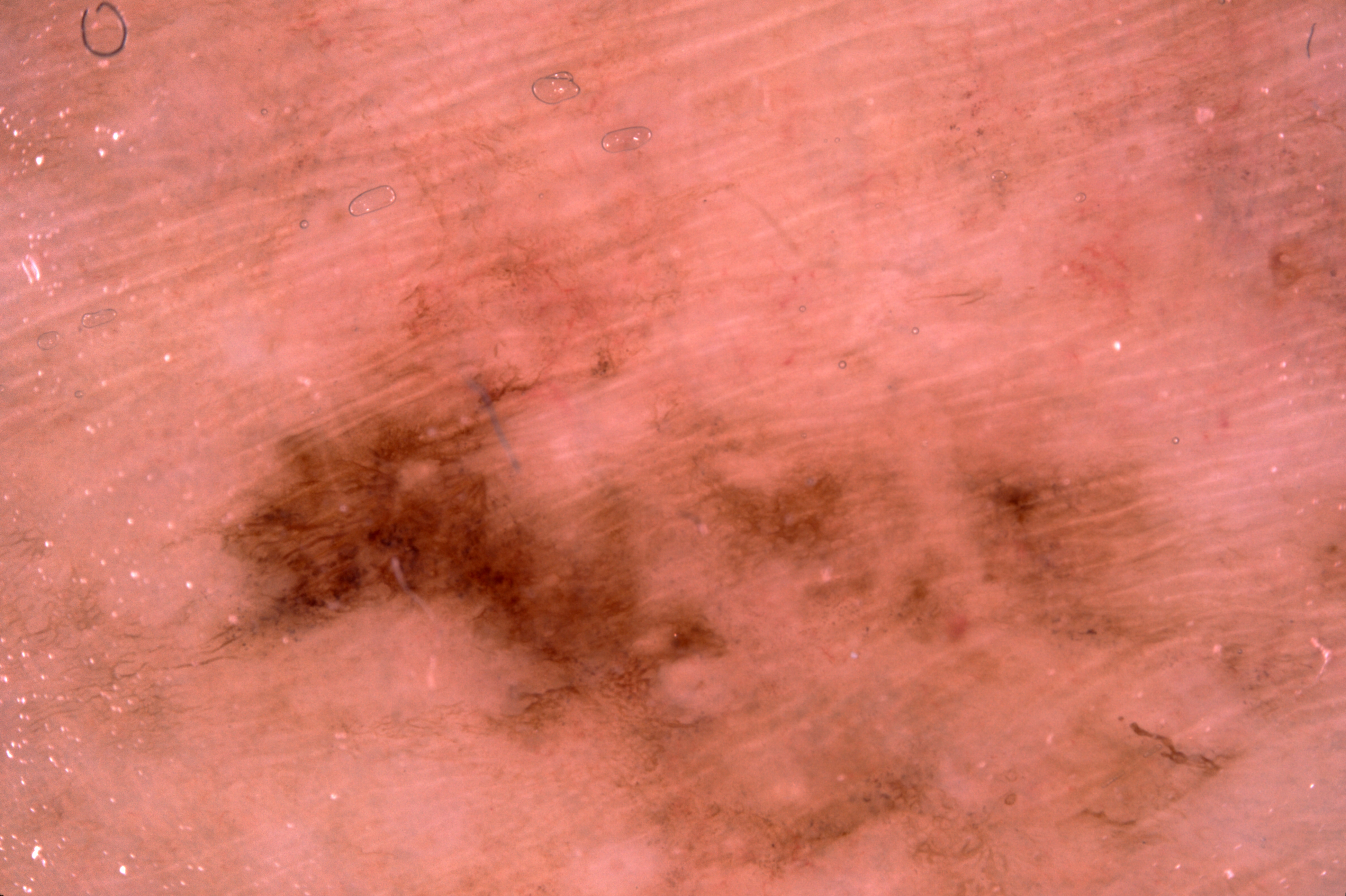A dermatoscopic image of a skin lesion.
In (x1, y1, x2, y2) order, the lesion is located at bbox(193, 297, 1247, 895).
Histopathologically confirmed as a melanoma.